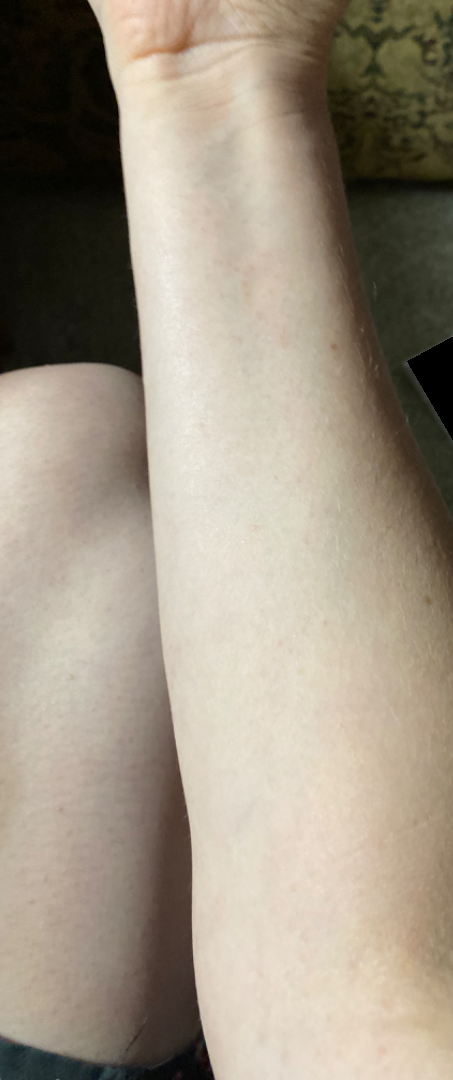| key | value |
|---|---|
| assessment | not assessable |
| lesion texture | raised or bumpy |
| anatomic site | arm |
| self-categorized as | skin that appeared healthy to them |
| patient-reported symptoms | bothersome appearance |
| shot type | at a distance |